The photo was captured at an angle; the affected area is the head or neck:
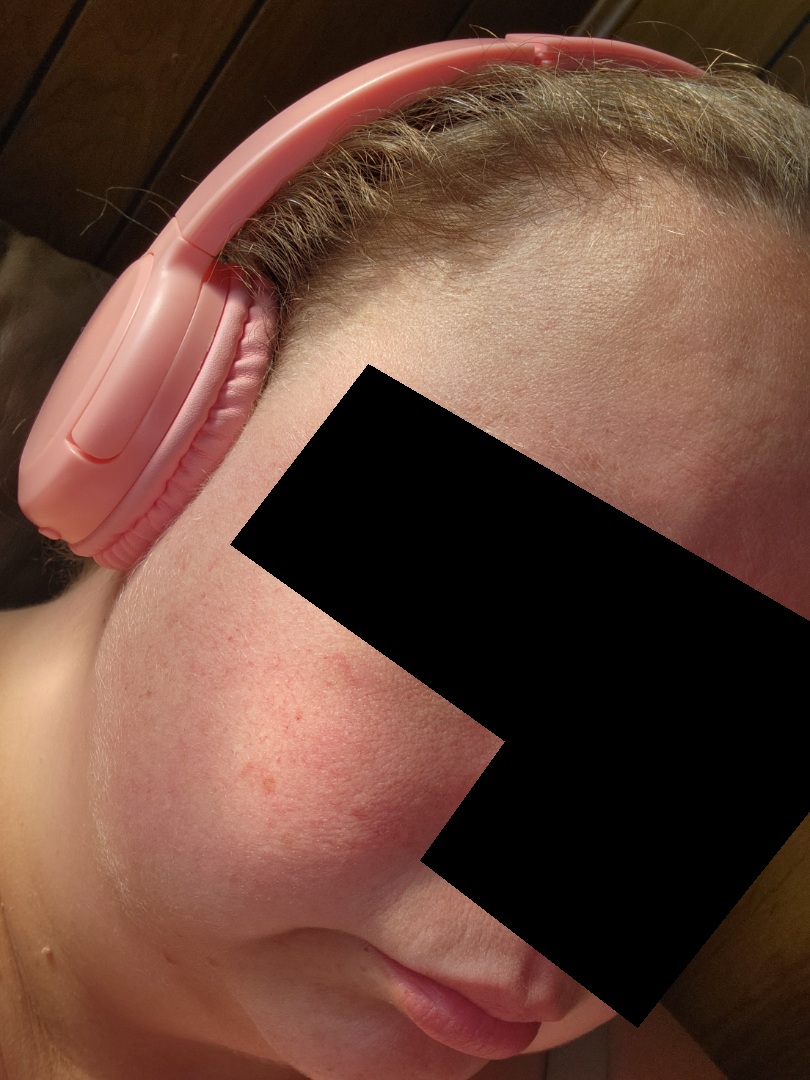The skin condition could not be confidently assessed from this image. Present for one to four weeks. Skin tone: FST I.